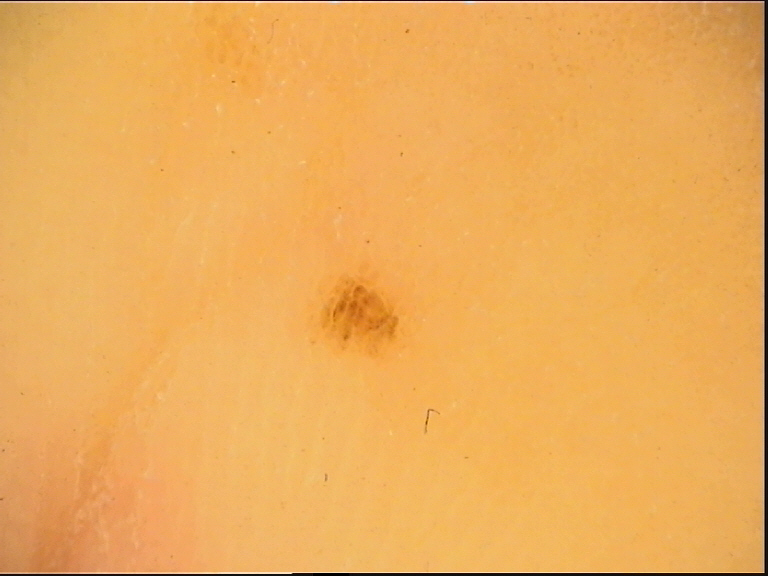Findings:
A dermoscopic image of a skin lesion.
Conclusion:
Labeled as an acral junctional nevus.